A dermoscopic close-up of a skin lesion.
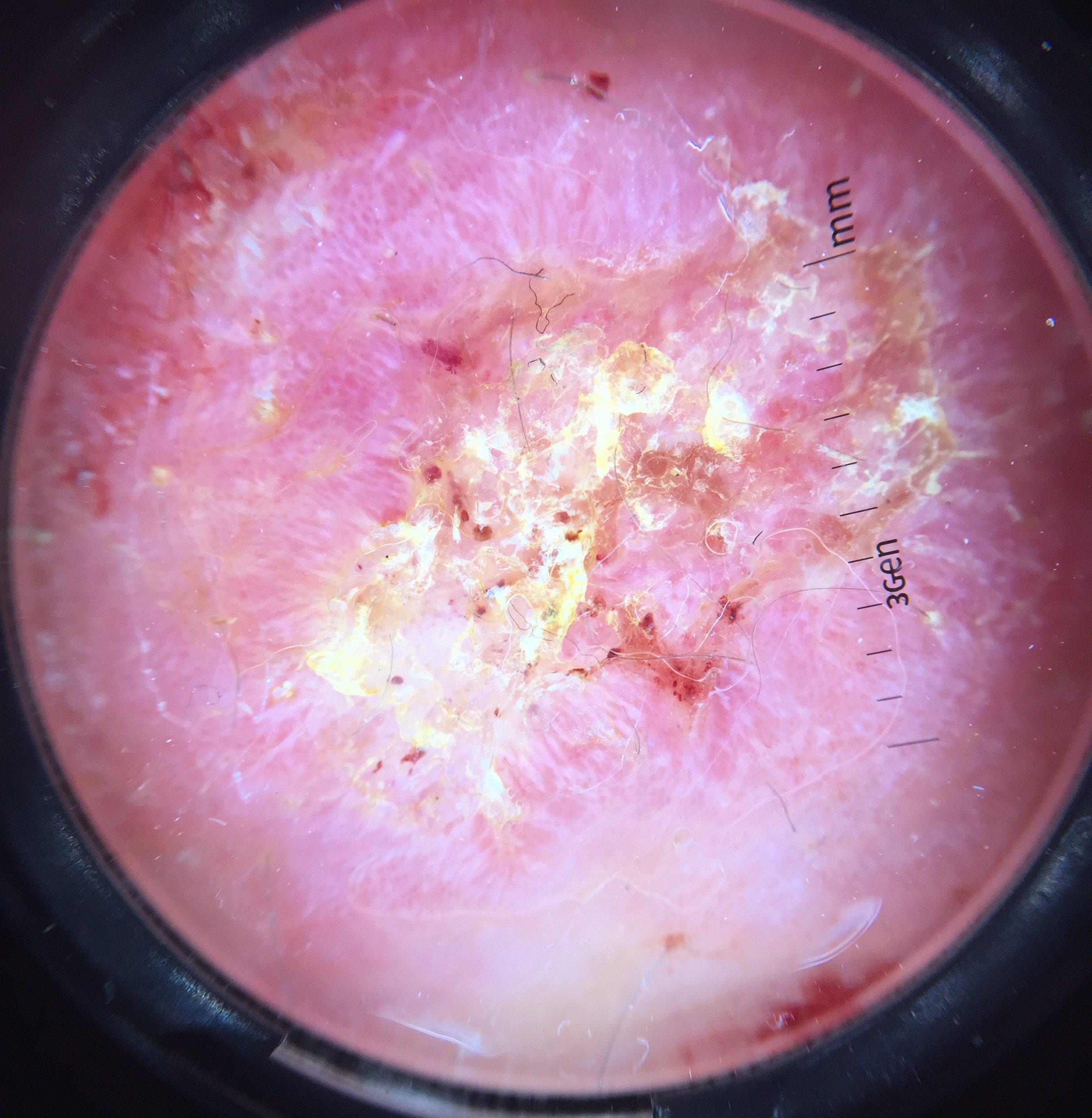{"diagnosis": {"name": "squamous cell carcinoma", "code": "scc", "malignancy": "malignant", "super_class": "non-melanocytic", "confirmation": "histopathology"}}